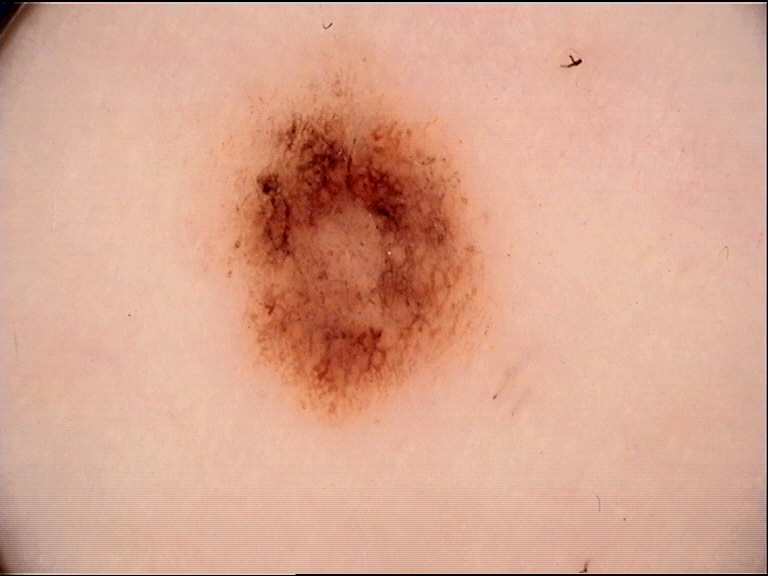modality: dermoscopy; diagnostic label: dysplastic junctional nevus (expert consensus).